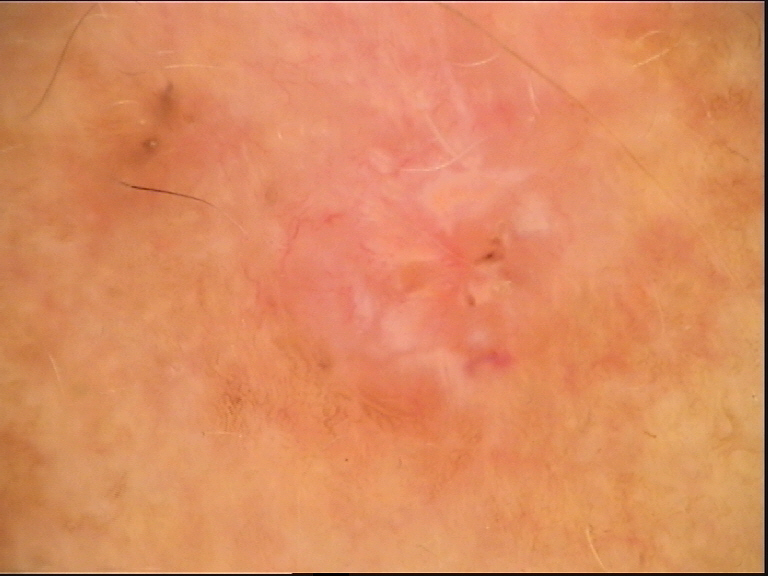A dermatoscopic image of a skin lesion. The architecture is that of a keratinocytic lesion. Histopathology confirmed a malignancy — a basal cell carcinoma.